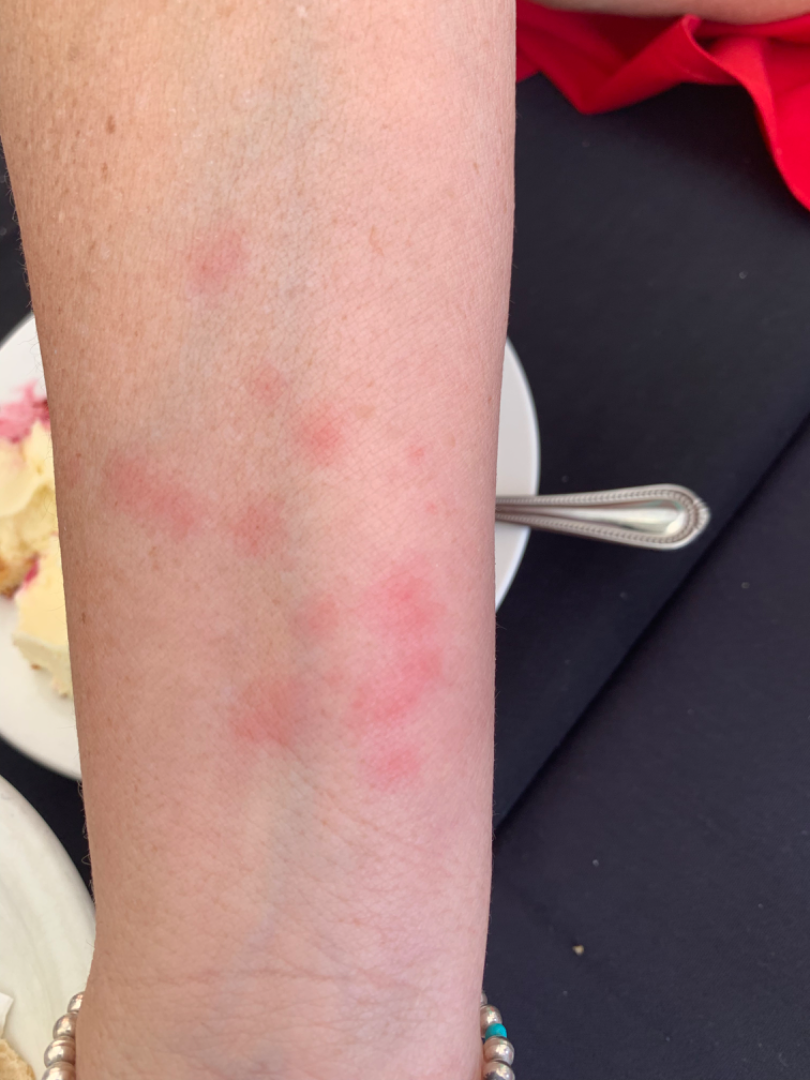• assessment — Insect Bite (most likely); Urticaria (possible); Allergic Contact Dermatitis (possible)